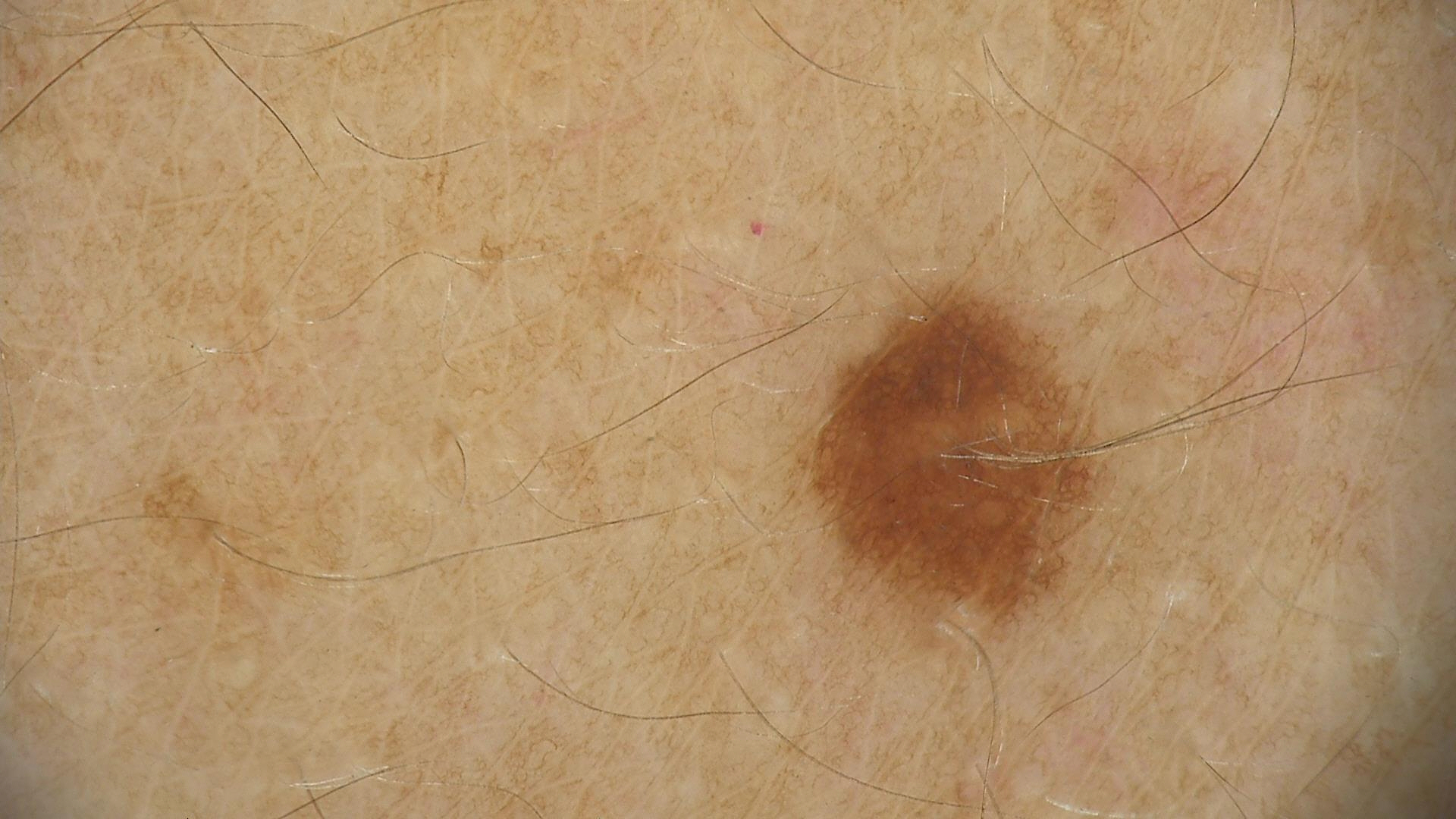Dermoscopy of a skin lesion. The diagnosis was a dysplastic junctional nevus.